A dermoscopic photograph of a skin lesion: 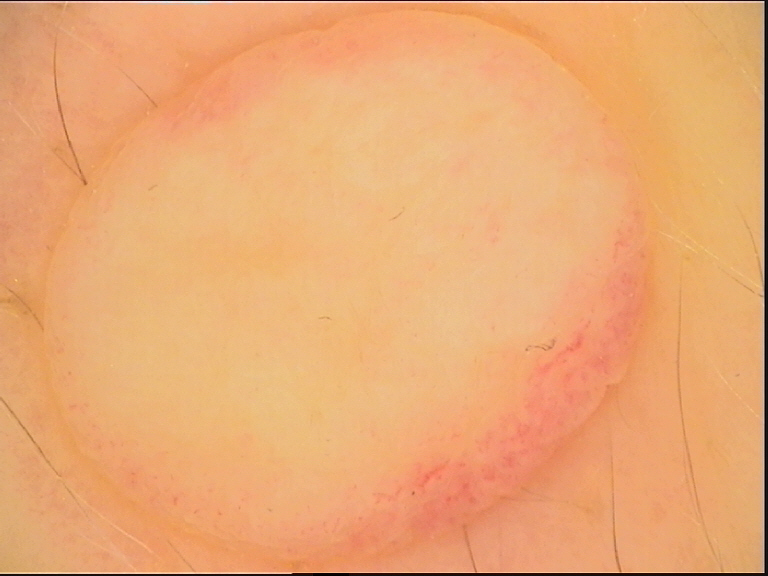Labeled as a banal lesion — a dermal nevus.